A female patient about 50 years old:
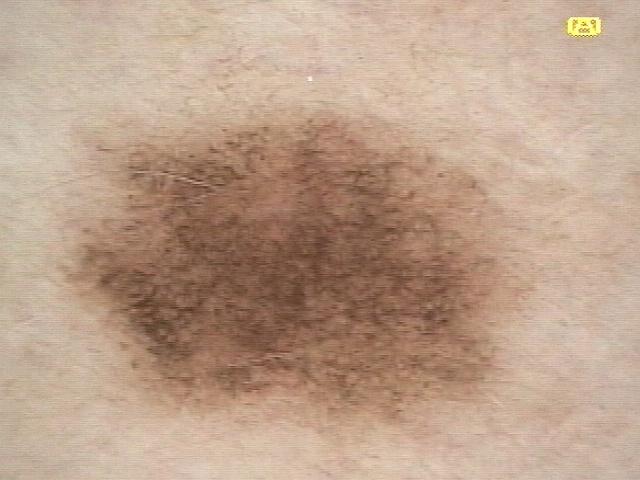location: an upper extremity, assessment: Nevus.